The patient reports itching and bothersome appearance · an image taken at an angle · located on the arm · lay reviewers estimated MST 8 (US pool) or 6 (India pool) · the patient described the issue as a rash — 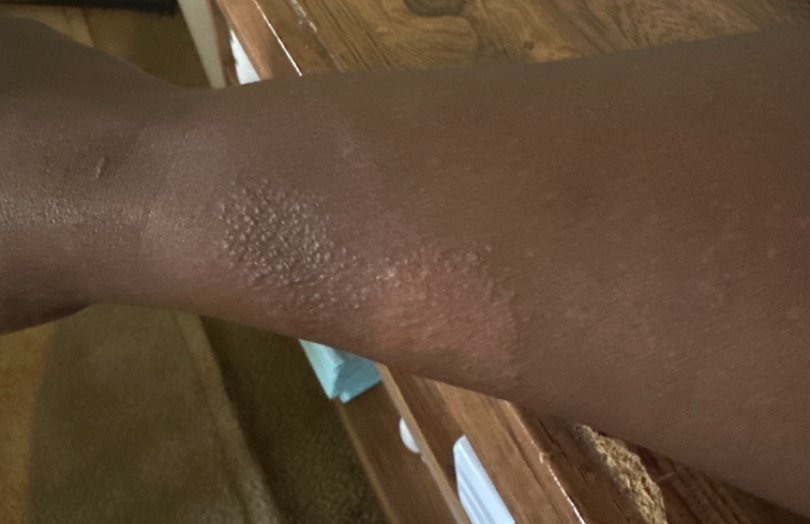| feature | finding |
|---|---|
| assessment | could not be assessed |